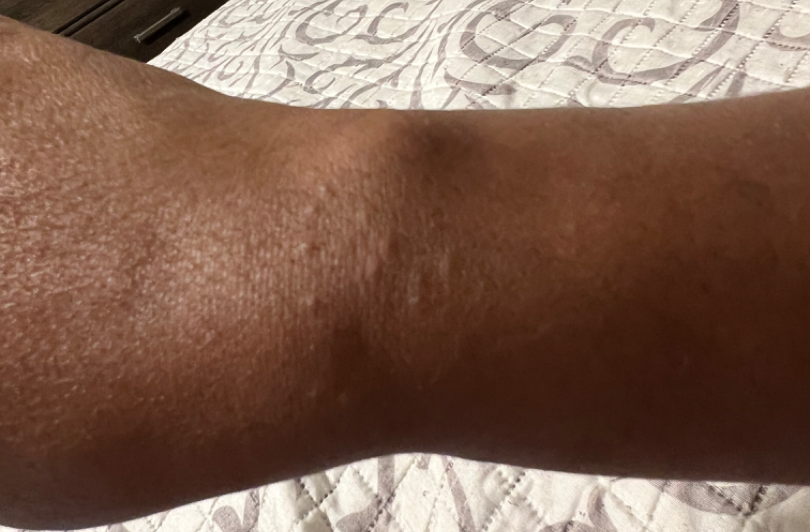The patient considered this a rash.
Symptoms reported: itching.
A close-up photograph.
The patient indicates the lesion is raised or bumpy.
Present for about one day.
The back of the hand is involved.
Reviewed remotely by one dermatologist: the leading consideration is Allergic Contact Dermatitis; the differential also includes Irritant Contact Dermatitis.